A dermoscopy image of a single skin lesion. A male subject aged 83 or older — 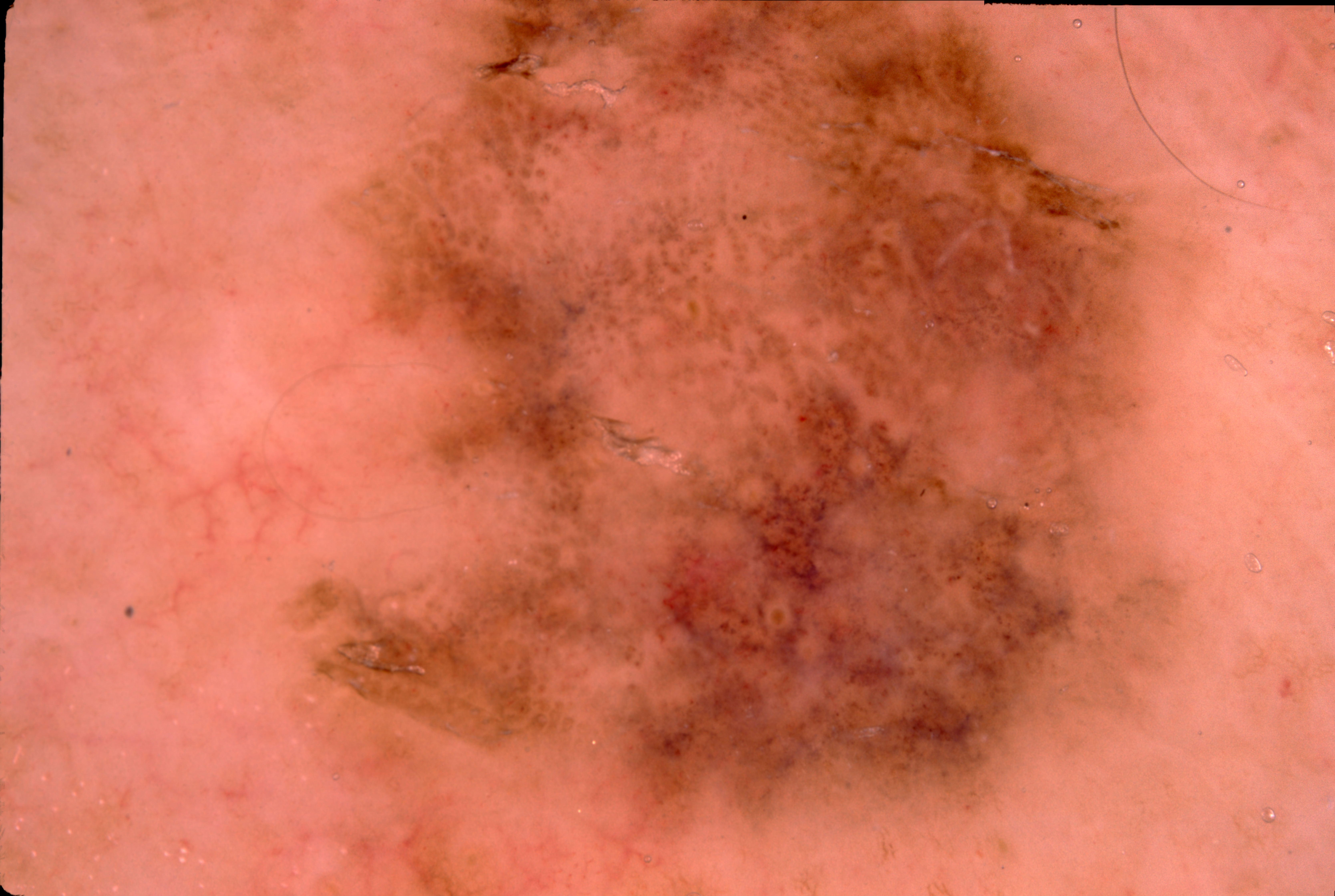dermoscopic_features:
  present:
    - negative network
    - milia-like cysts
  absent:
    - pigment network
    - streaks
frame_clip: lesion extends past the field edge
lesion_extent:
  approx_field_fraction_pct: 45
lesion_location:
  bbox_xyxy:
    - 293
    - 0
    - 1182
    - 843
diagnosis:
  name: melanoma
  malignancy: malignant
  lineage: melanocytic
  provenance: histopathology